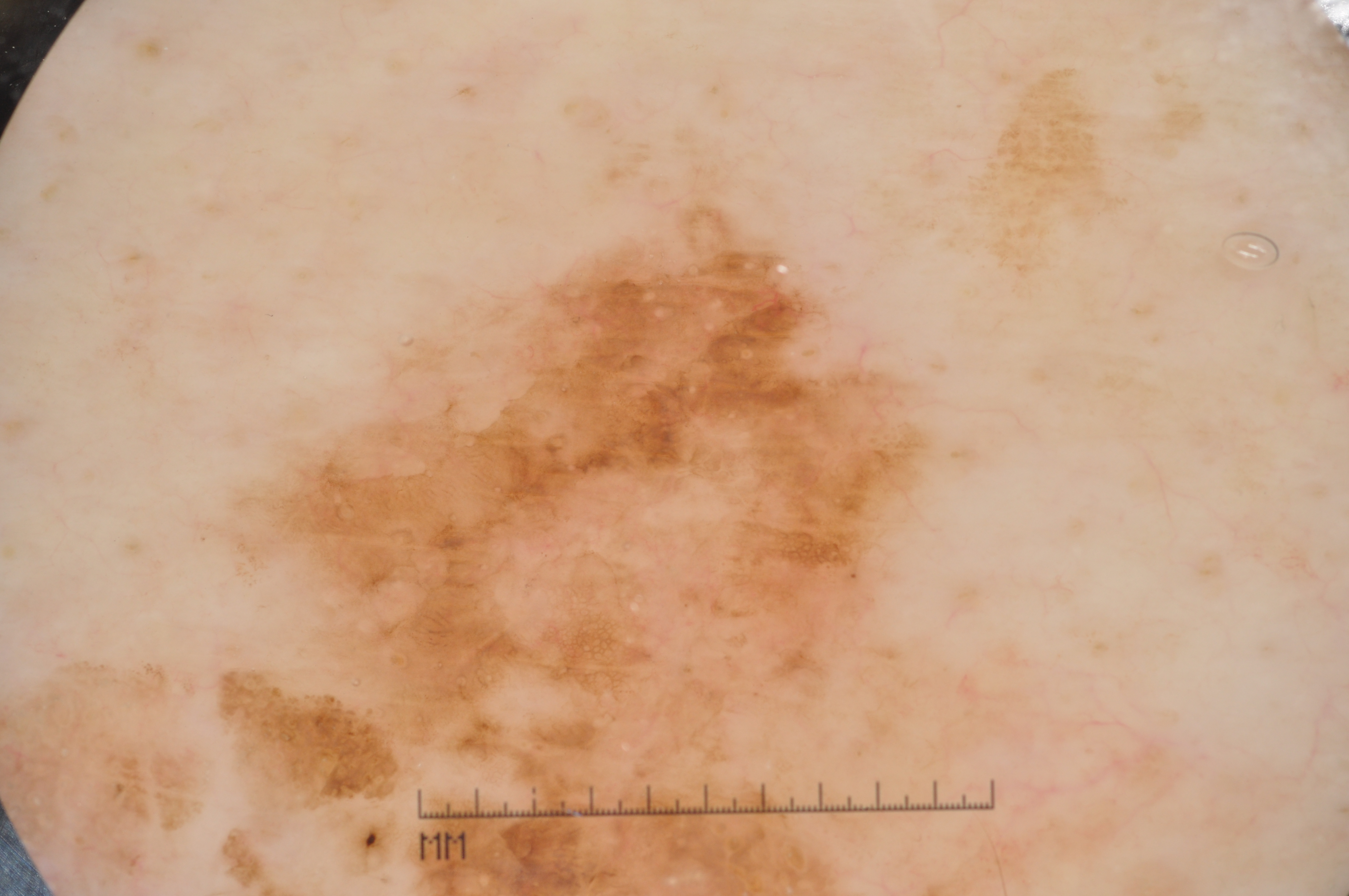patient = male, approximately 80 years of age
image = dermoscopy
dermoscopic features = pigment network, milia-like cysts, and negative network
bounding box = 172 73 986 790
diagnostic label = a melanoma